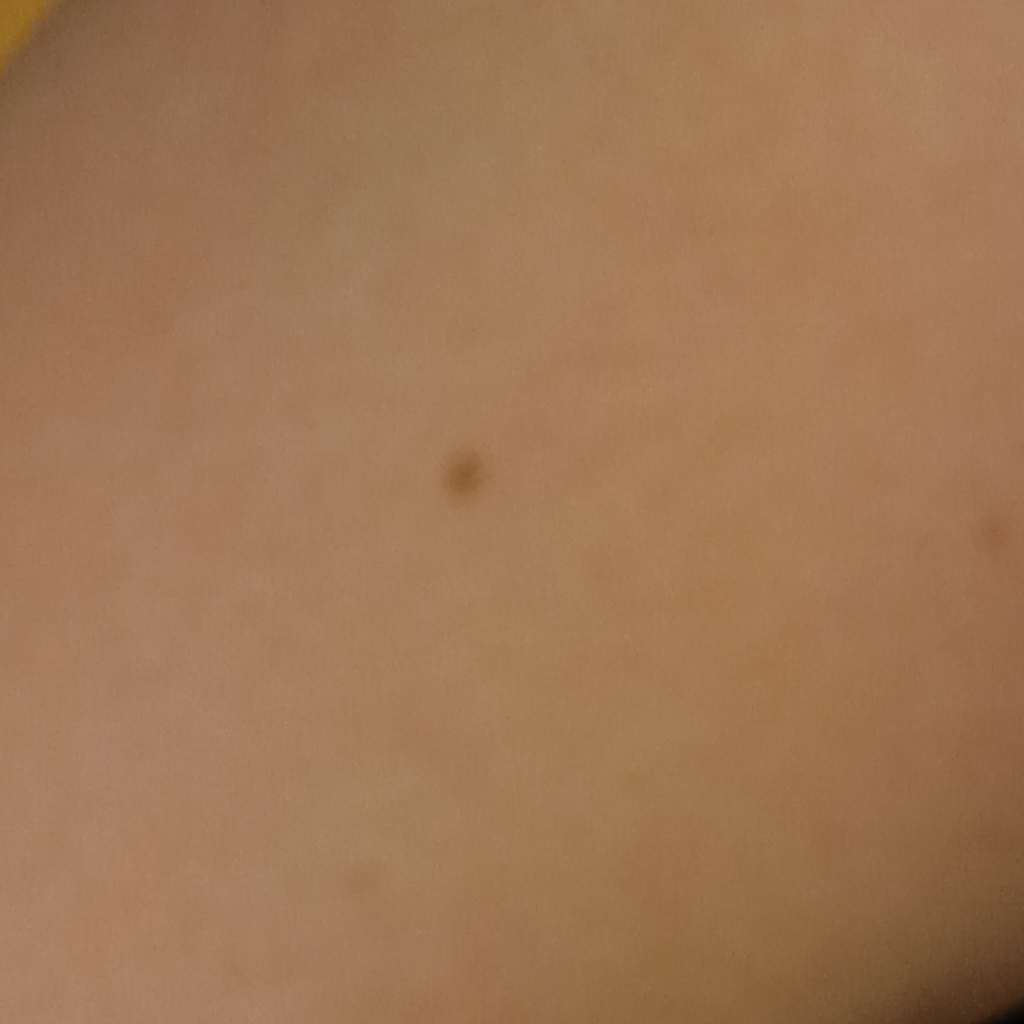The dermatologists' assessment was a melanocytic nevus.